Dermoscopy of a skin lesion:
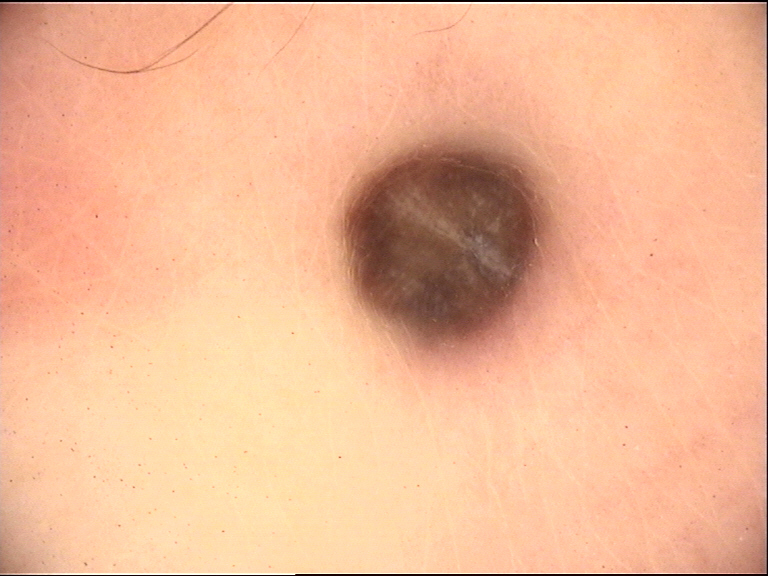| field | value |
|---|---|
| diagnostic label | blue nevus (expert consensus) |